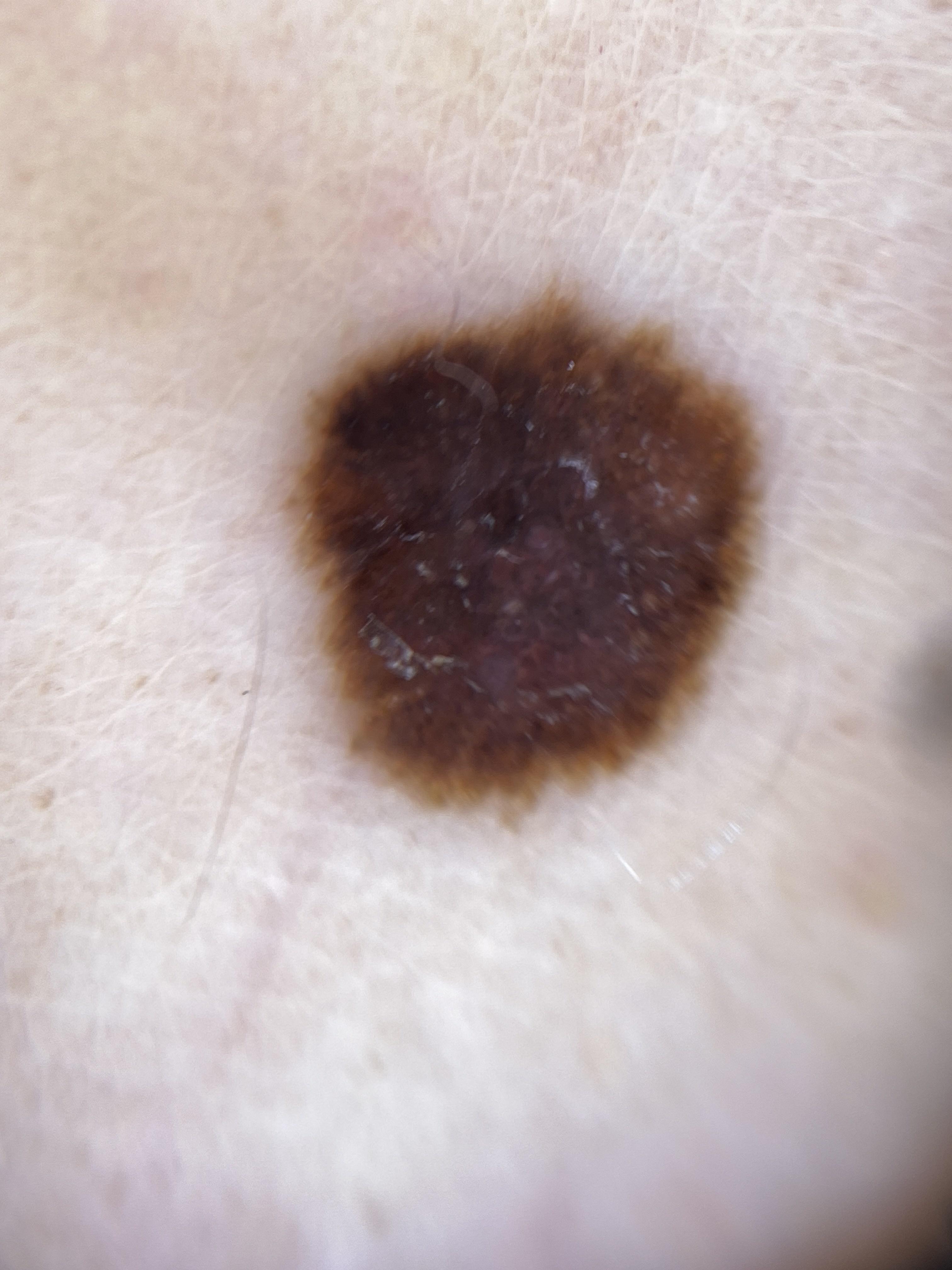The patient is FST II. The chart documents a prior melanoma. A female patient roughly 40 years of age. A dermoscopic image of a skin lesion. On biopsy, the diagnosis was a melanoma.